The contributor is a male aged 18–29, the photo was captured at an angle.
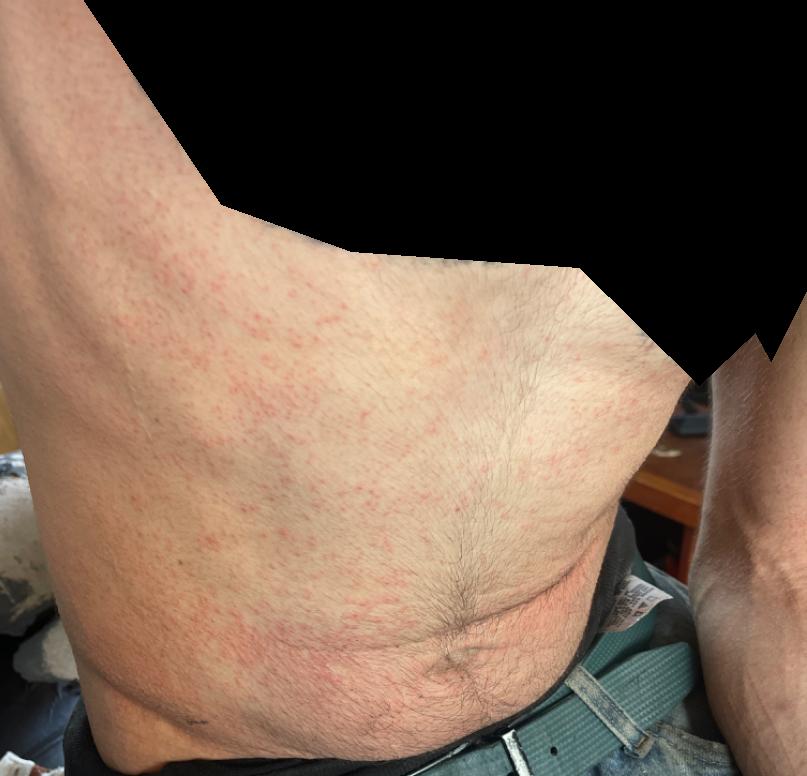skin_tone:
  monk_skin_tone: 3
differential:
  leading:
    - Drug Rash
  considered:
    - Viral Exanthem
  unlikely:
    - Hypersensitivity